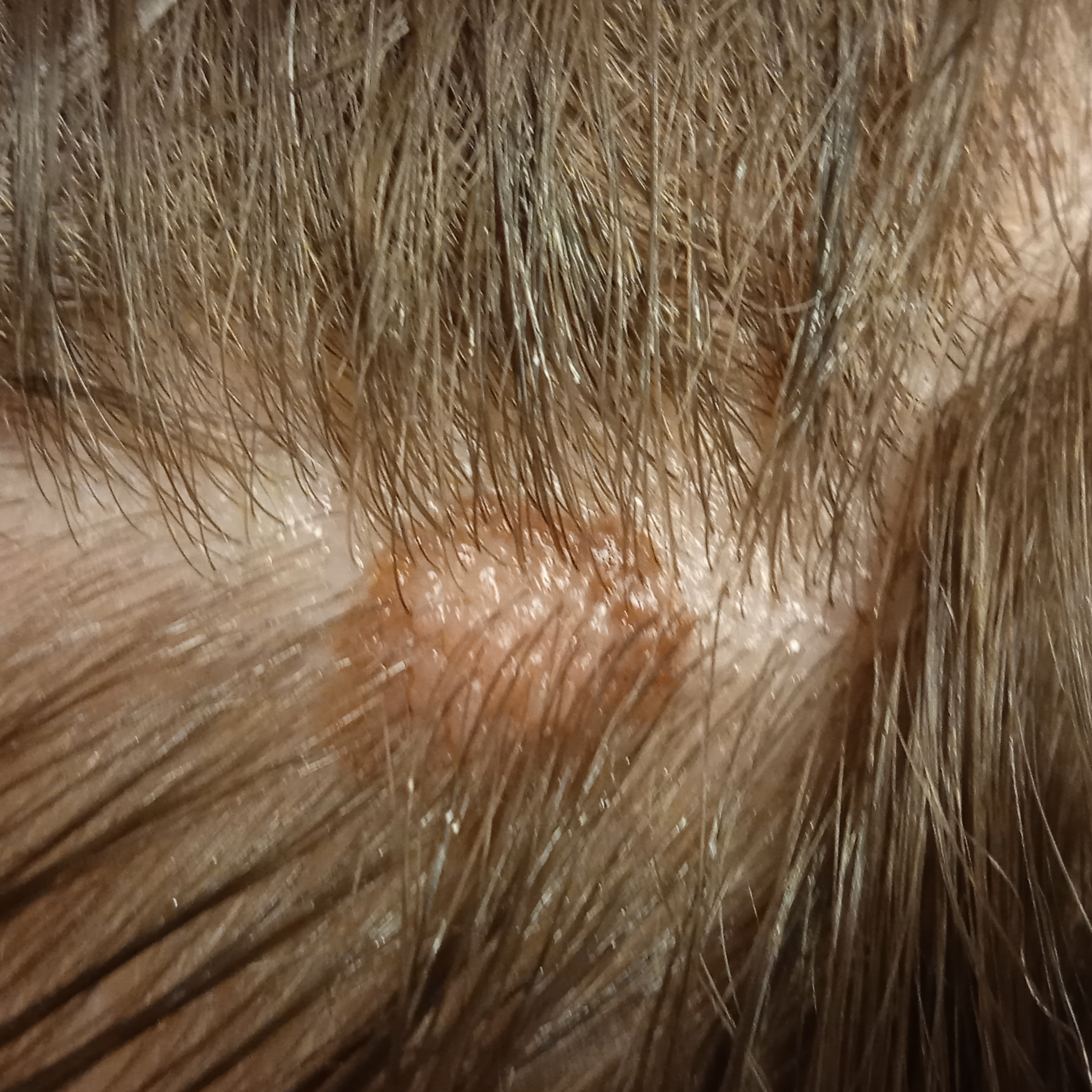A female subject 15 years of age.
A clinical photograph of a skin lesion.
The patient says their skin reddens with sun exposure.
The patient describes having few moles overall.
Acquired for a research image collection, with no referral diagnosis.
The lesion is on the head.
The lesion is about 9.1 mm across.
The lesion was assessed as a melanocytic nevus.